The contributor reports itching; the lesion involves the front of the torso and back of the torso; skin tone: FST III; the patient is a female aged 18–29; an image taken at a distance; the condition has been present for one to four weeks; the contributor reports the lesion is raised or bumpy — 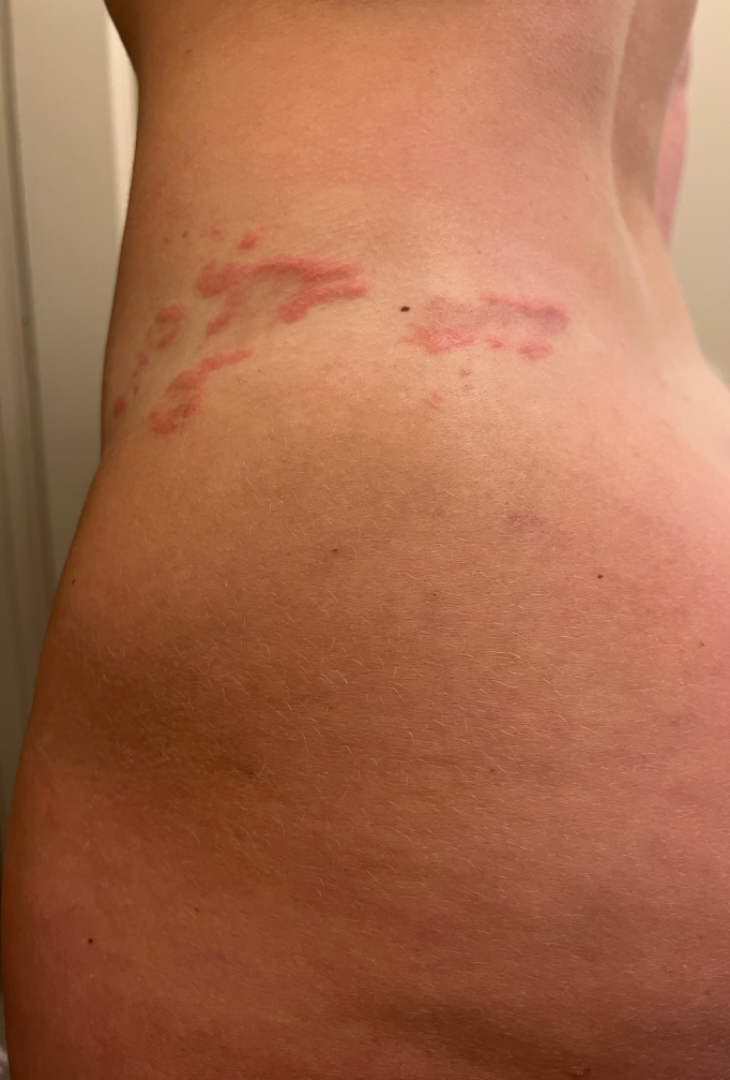dermatologist impression — Granuloma annulare (possible); Pemphigoid gestationis (possible); Pruritic urticarial papules and plaques of pregnancy (possible).